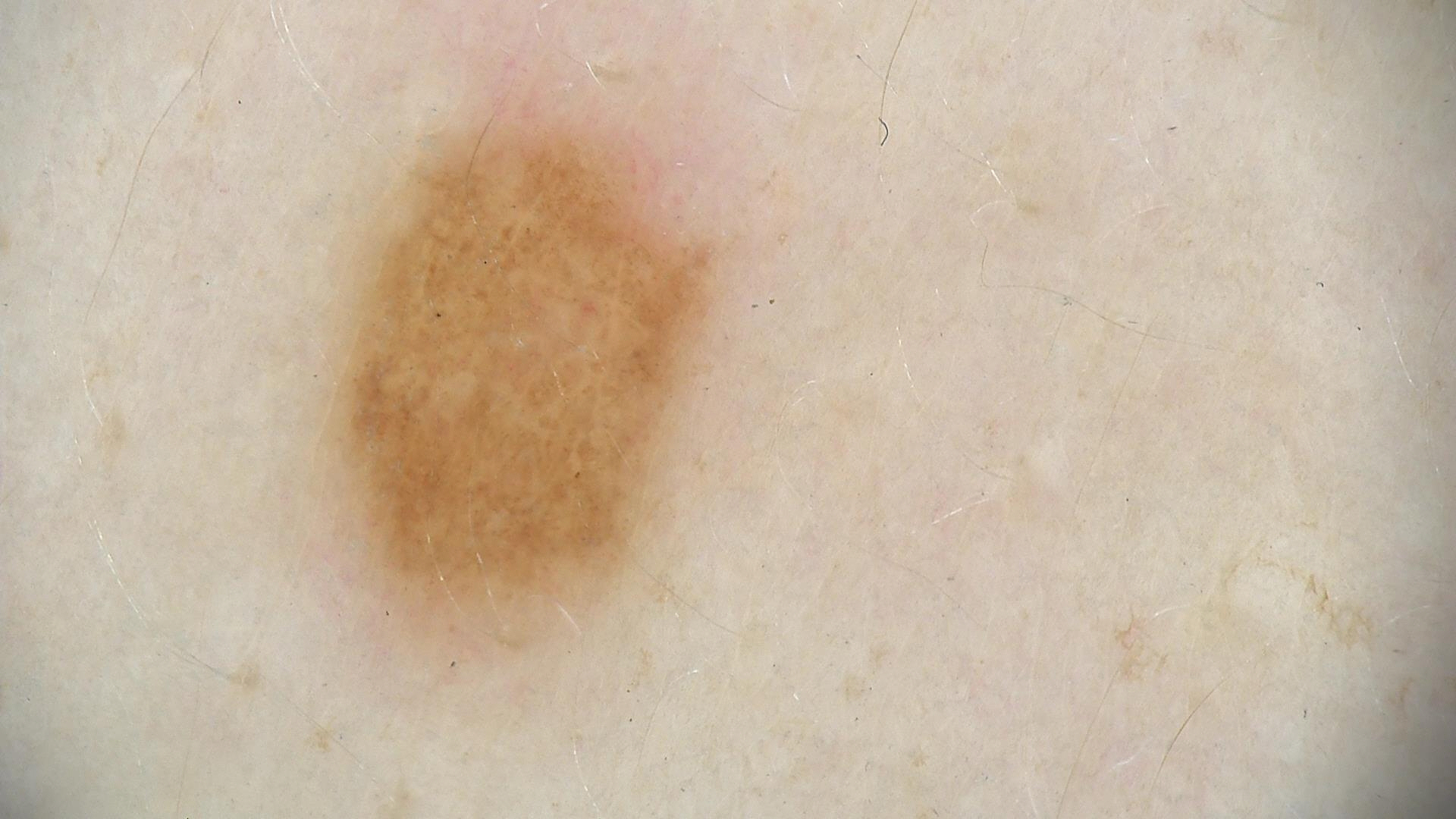Consistent with a dysplastic junctional nevus.